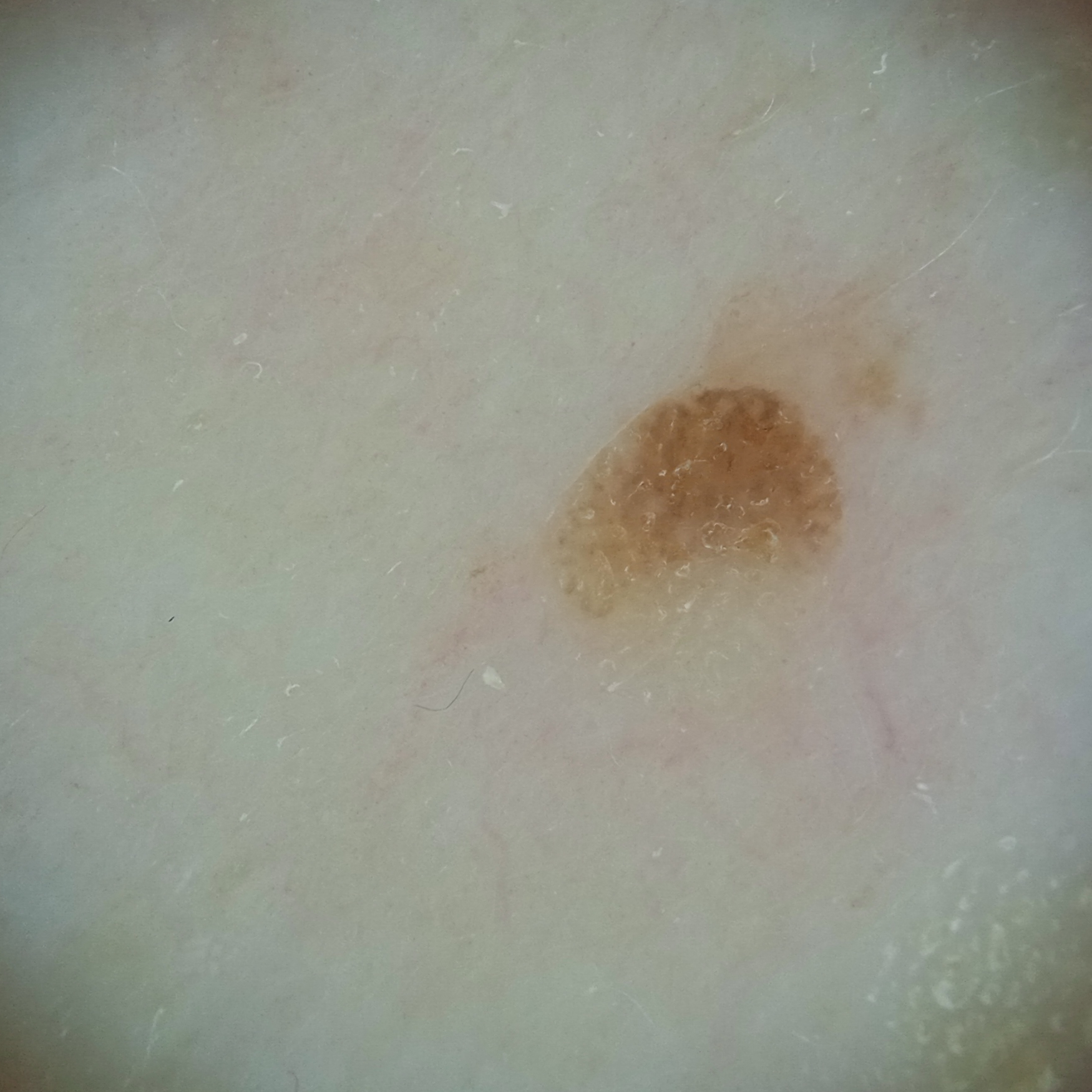• risk factors — a personal history of cancer, a personal history of skin cancer, no sunbed use, no immunosuppression
• subject — male, aged 77
• nevus count — a moderate number of melanocytic nevi
• sun reaction — skin reddens with sun exposure
• site — the back
• diagnosis — seborrheic keratosis (dermatologist consensus)